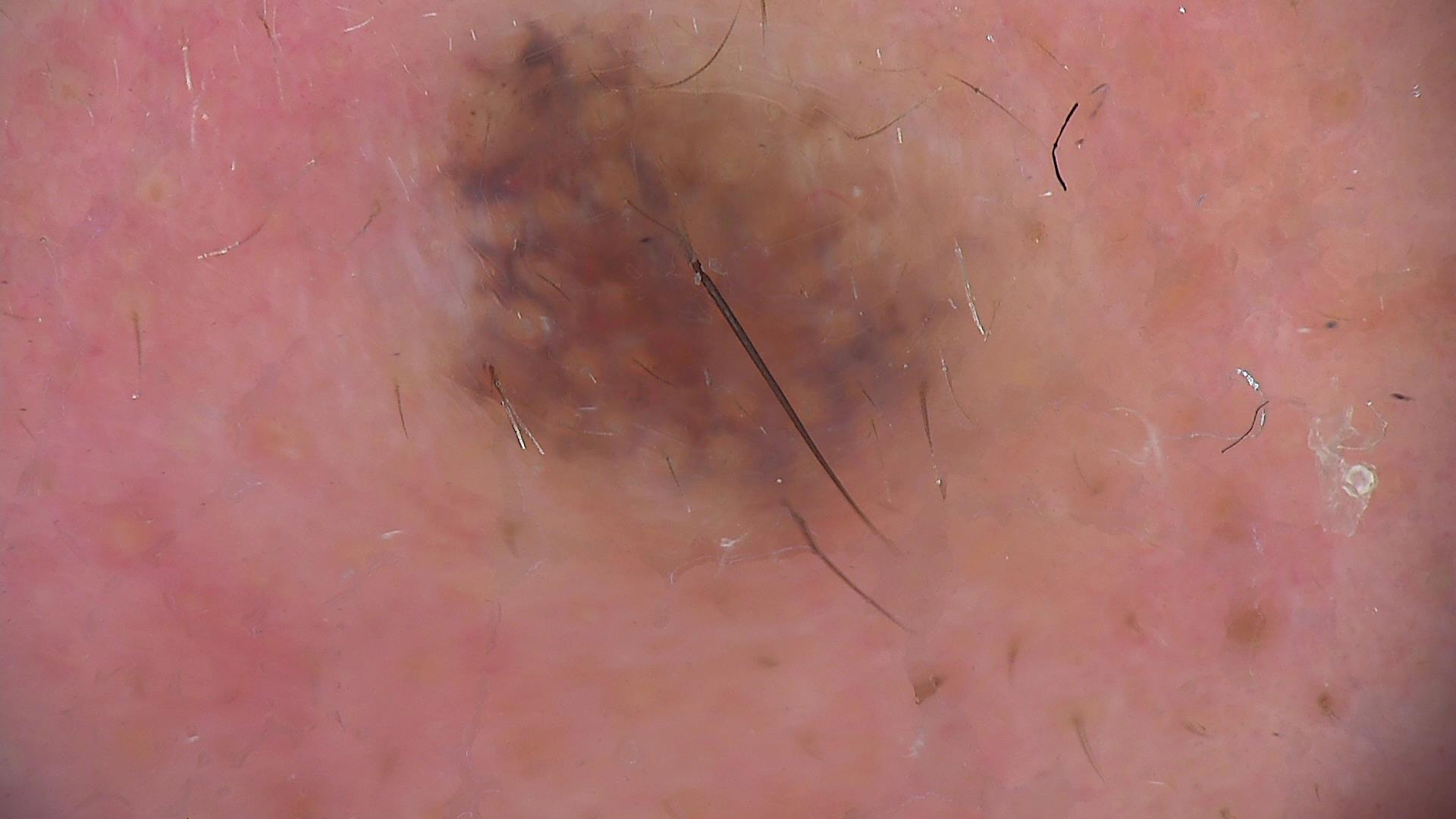Consistent with a Miescher nevus.